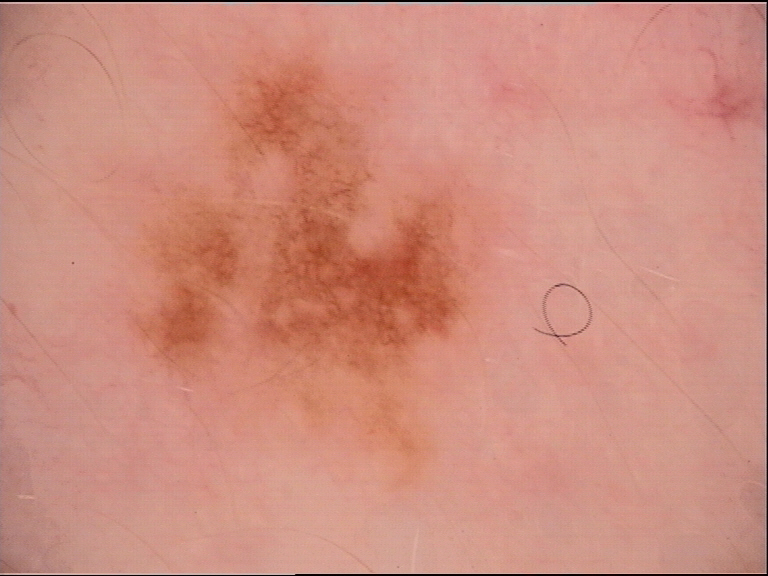class: dysplastic junctional nevus (expert consensus).